Symptoms reported: itching · texture is reported as raised or bumpy · the contributor notes the condition has been present for less than one week · self-categorized by the patient as a rash · this image was taken at an angle · located on the arm — 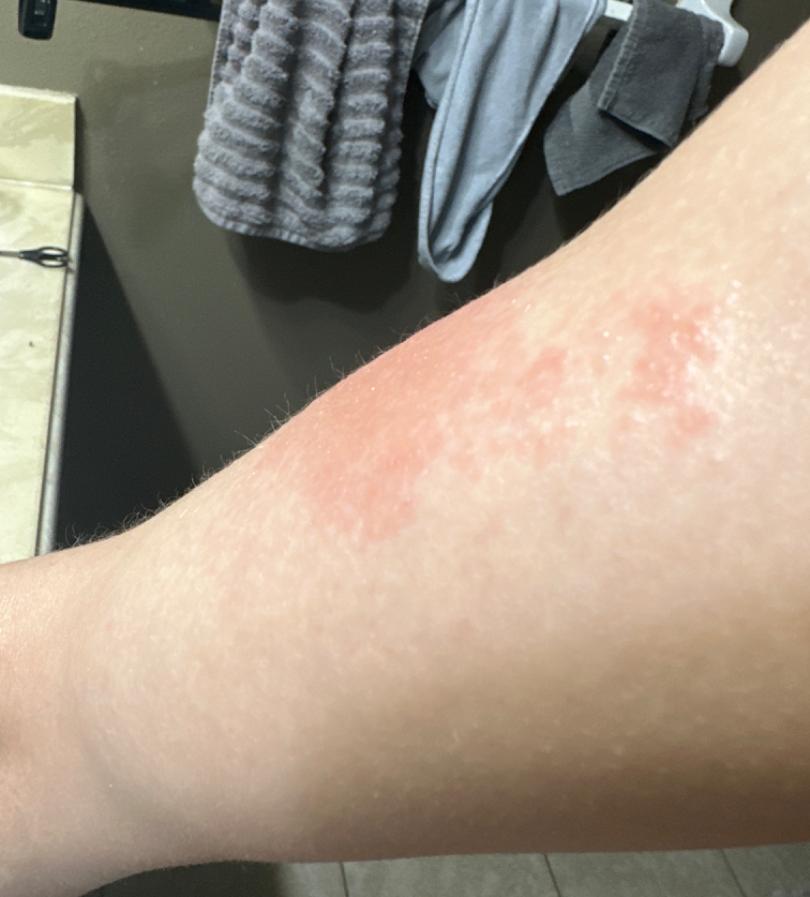Impression: On remote review of the image, the leading consideration is Allergic Contact Dermatitis; also consider Acute dermatitis, NOS.